A close-up photograph; no relevant systemic symptoms; the patient described the issue as skin that appeared healthy to them; the subject is male; reported lesion symptoms include enlargement, itching and bothersome appearance; present for less than one week.
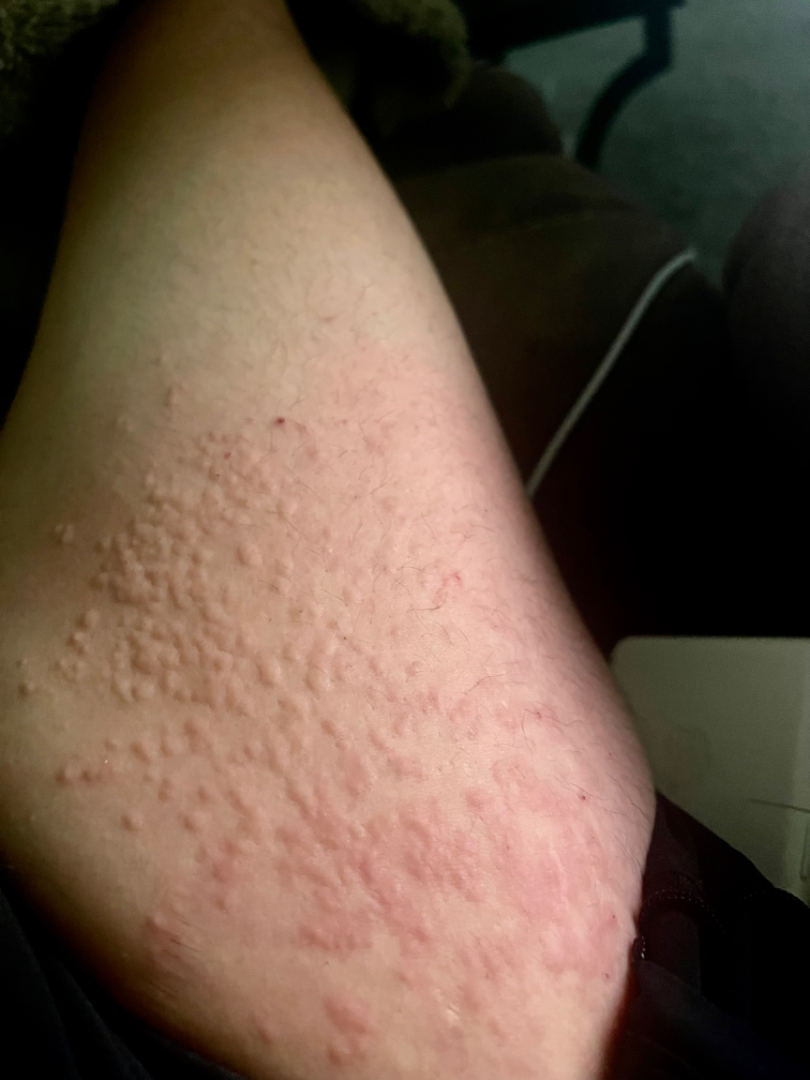Consistent with Urticaria.